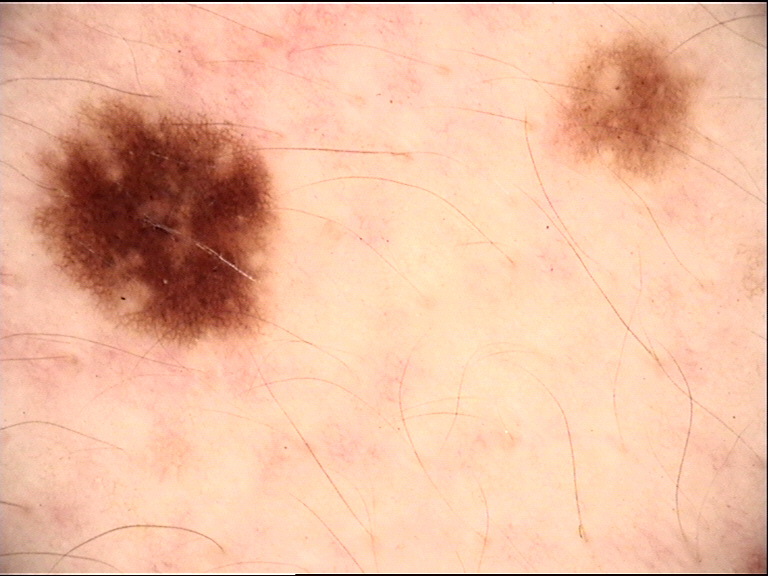Q: What was the diagnostic impression?
A: junctional nevus (expert consensus)